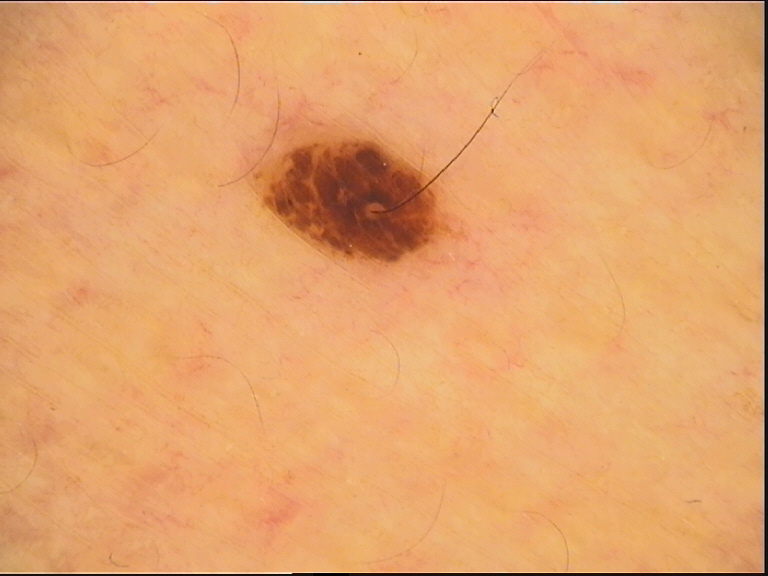A dermoscopic image of a skin lesion.
Labeled as a banal lesion — a compound nevus.